The arm is involved; male patient, age 18–29; an image taken at a distance — 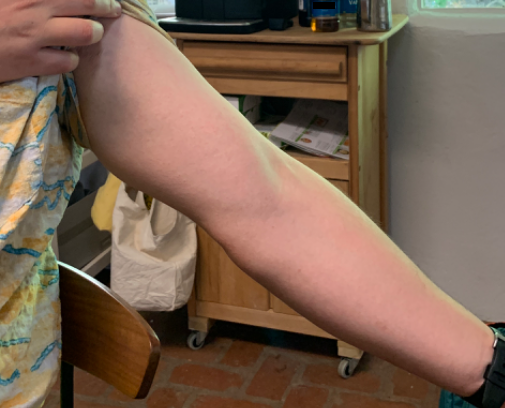dermatologist impression = most consistent with Eczema; also consider Keratosis pilaris.